A skin lesion imaged with a dermatoscope:
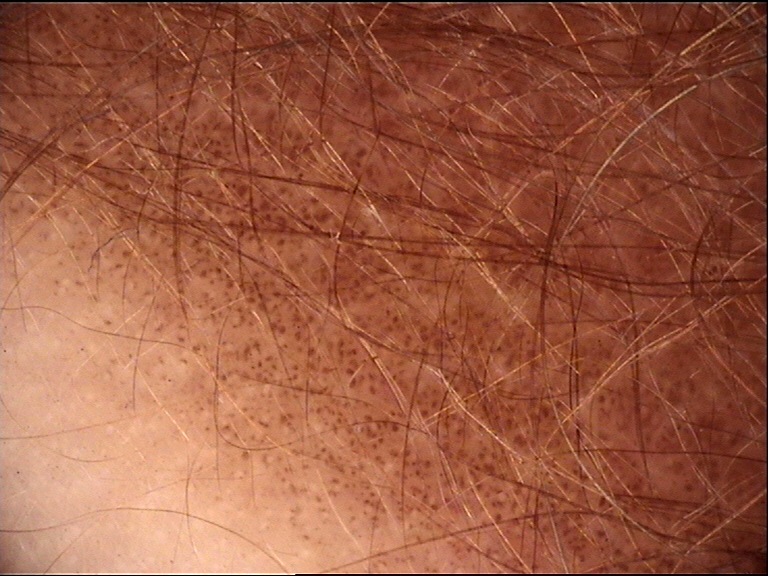  lesion_type:
    main_class: banal
    pattern: junctional
  diagnosis:
    name: congenital junctional nevus
    code: cjb
    malignancy: benign
    super_class: melanocytic
    confirmation: expert consensus